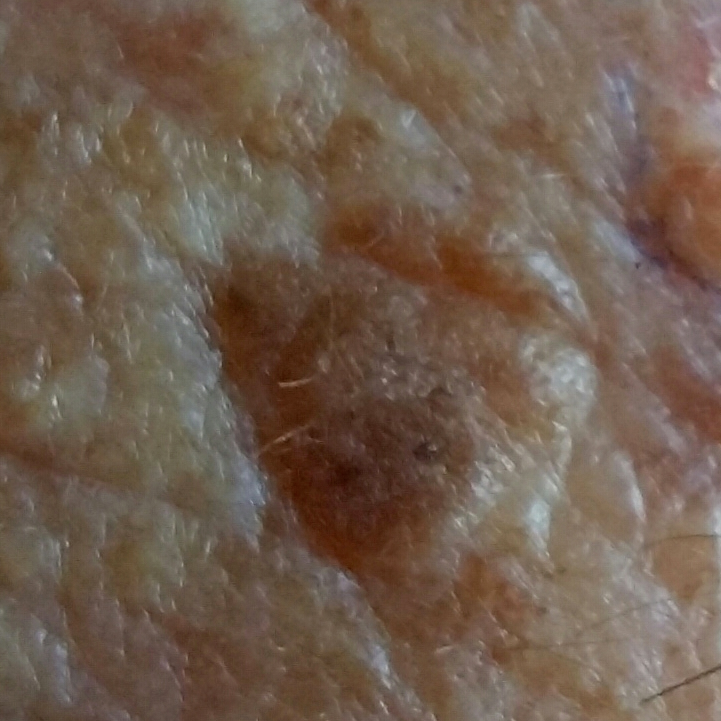Case summary:
A subject 64 years old. A clinical photo of a skin lesion taken with a smartphone. The lesion involves the face. The patient describes that the lesion is elevated and has grown, but does not hurt.
Impression:
The consensus clinical diagnosis was a seborrheic keratosis.